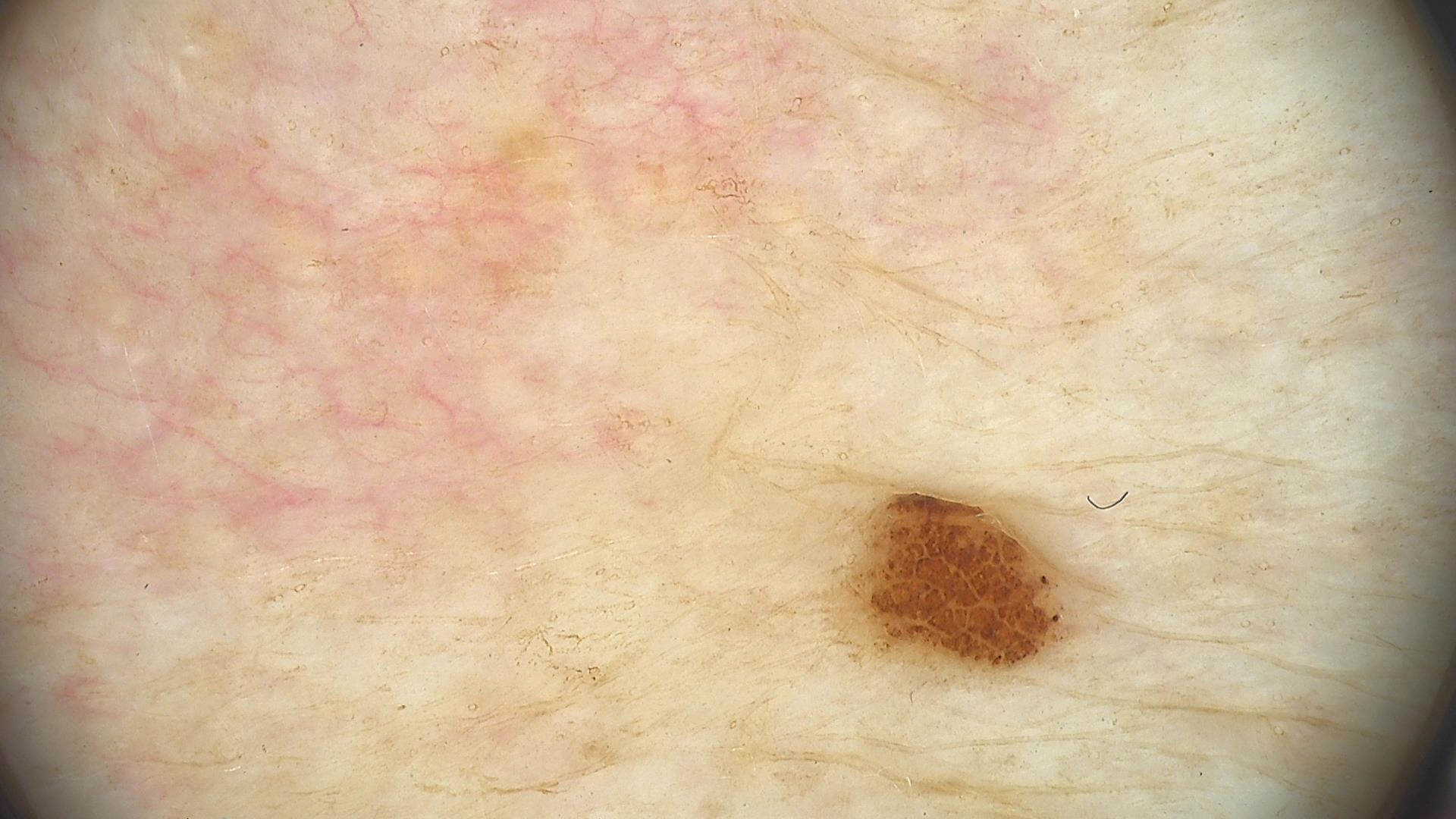A dermoscopic close-up of a skin lesion.
The diagnosis was a dysplastic junctional nevus.